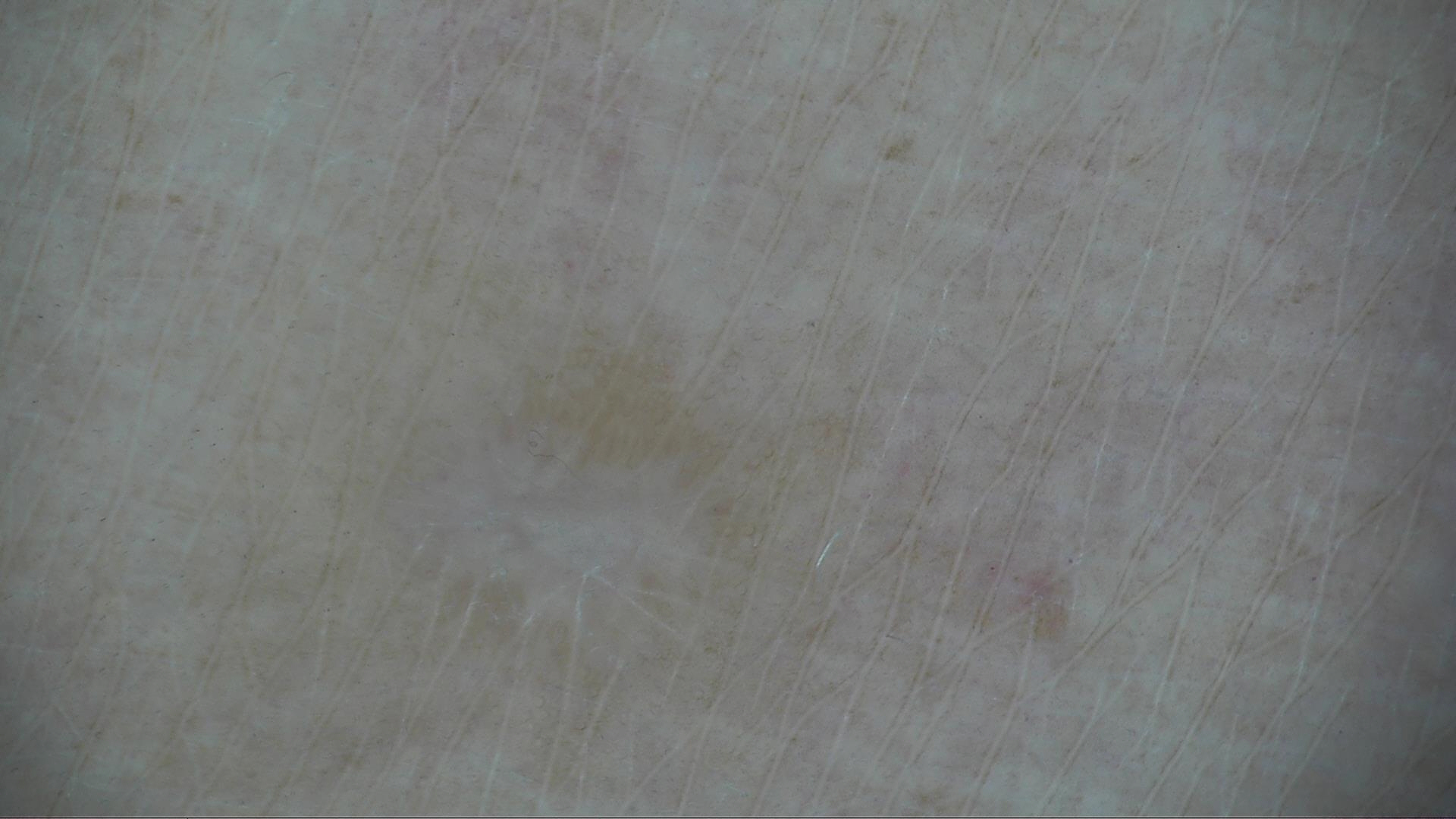image: dermoscopy
diagnosis:
  name: dermatofibroma
  code: df
  malignancy: benign
  super_class: non-melanocytic
  confirmation: expert consensus